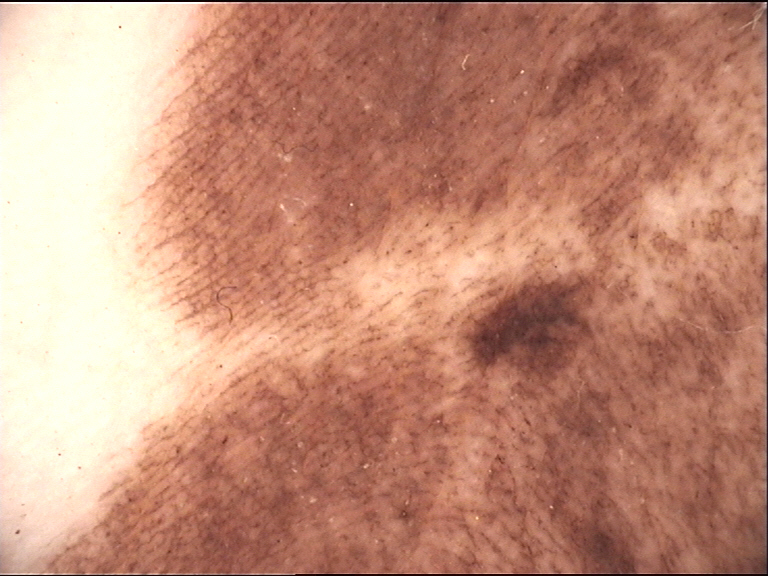image = dermoscopy; lesion type = banal; class = acral compound nevus (expert consensus).